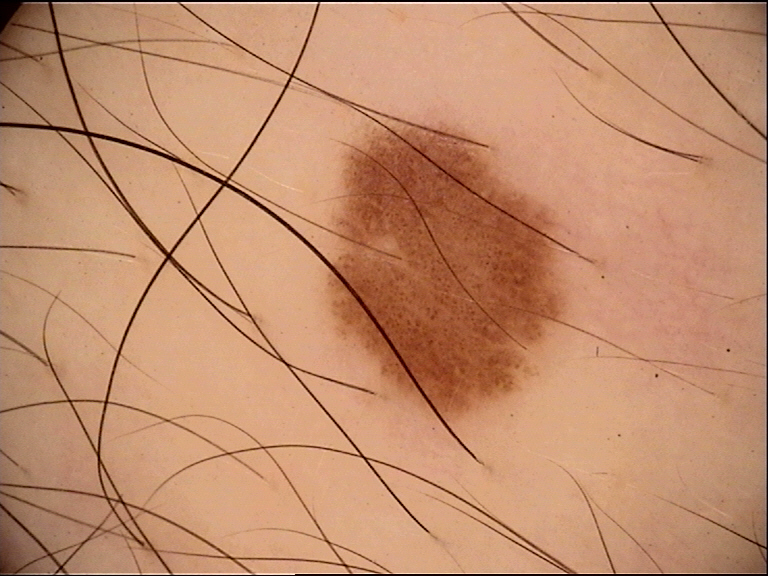Case:
A skin lesion imaged with a dermatoscope.
Impression:
The diagnosis was a dysplastic junctional nevus.